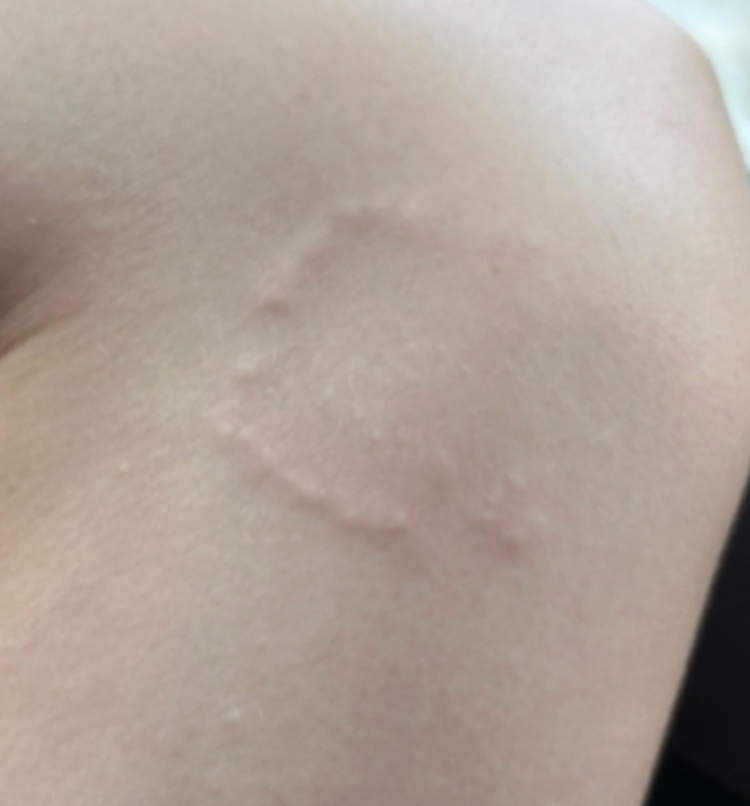| feature | finding |
|---|---|
| contributor | female, age 18–29 |
| framing | close-up |
| present for | one to three months |
| body site | leg |
| diagnostic considerations | the leading impression is Granuloma annulare |